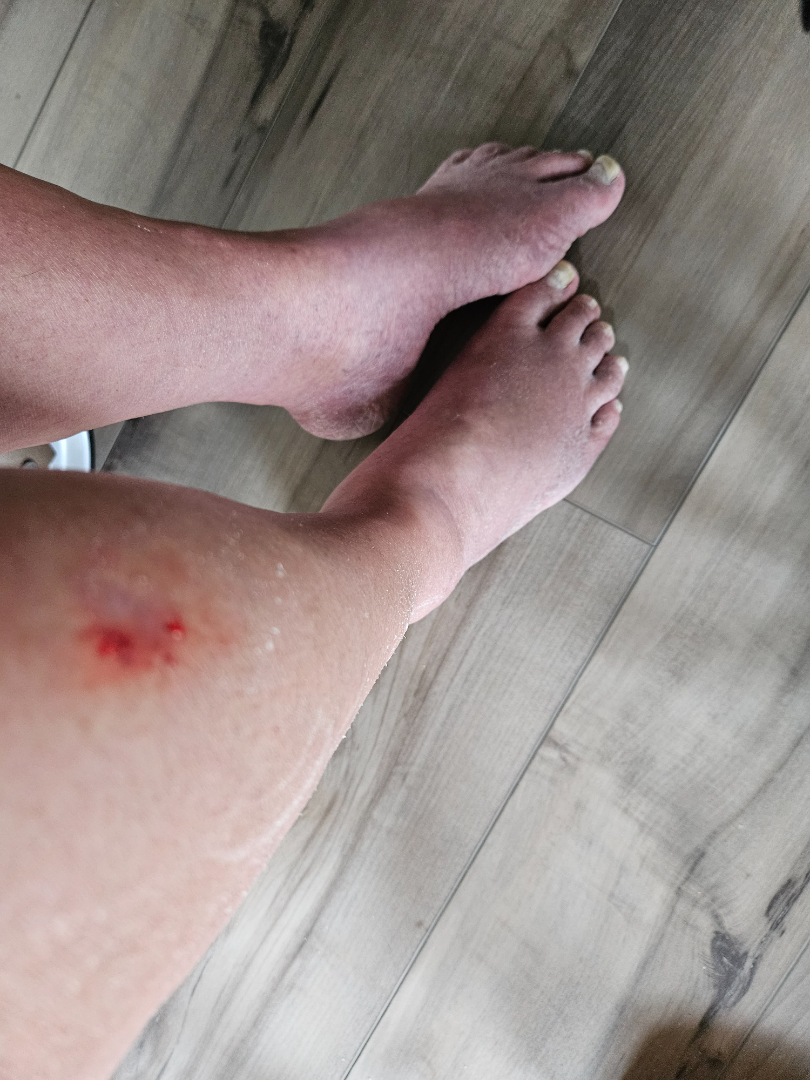| key | value |
|---|---|
| assessment | indeterminate from the photograph |
| lesion symptoms | enlargement and itching |
| contributor | male |
| skin tone | self-reported Fitzpatrick phototype IV |
| anatomic site | leg |
| photo taken | at an angle |